The photo was captured at an angle.
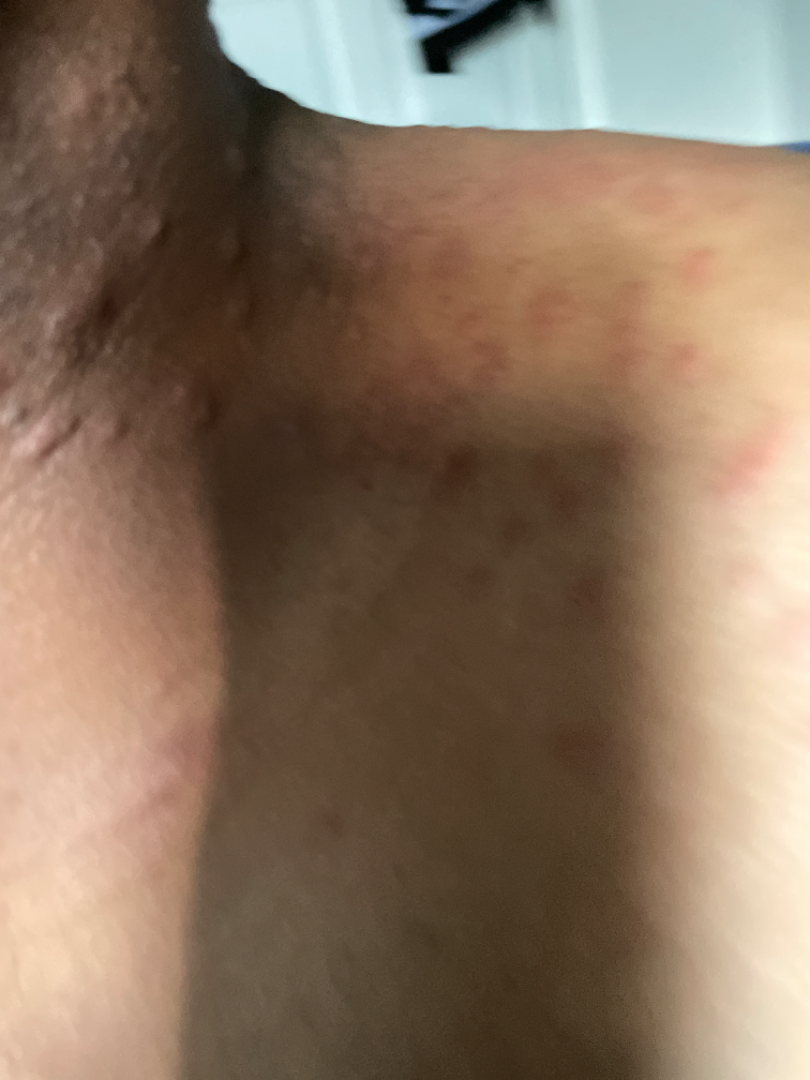Fitzpatrick phototype V; non-clinician graders estimated Monk Skin Tone 6 (US pool) or 4 (India pool).
Folliculitis, Insect Bite and Allergic Contact Dermatitis were considered with similar weight.